The lesion involves the leg; the photograph is a close-up of the affected area:
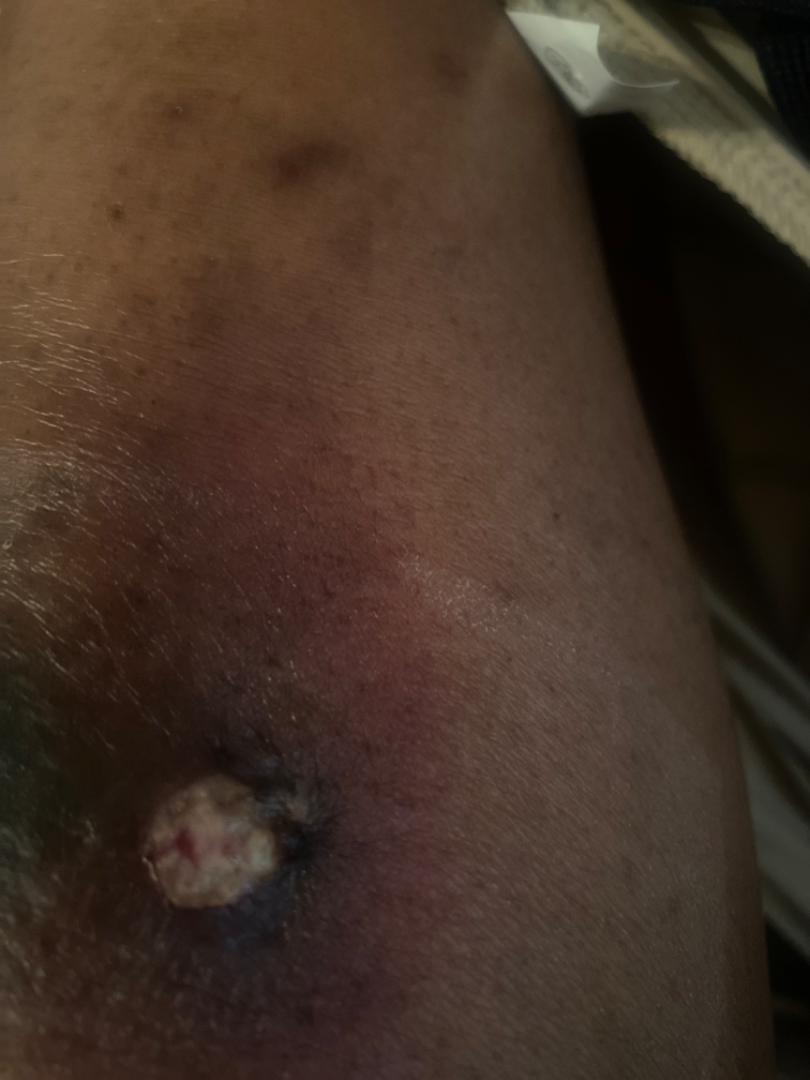The case was indeterminate on photographic review.